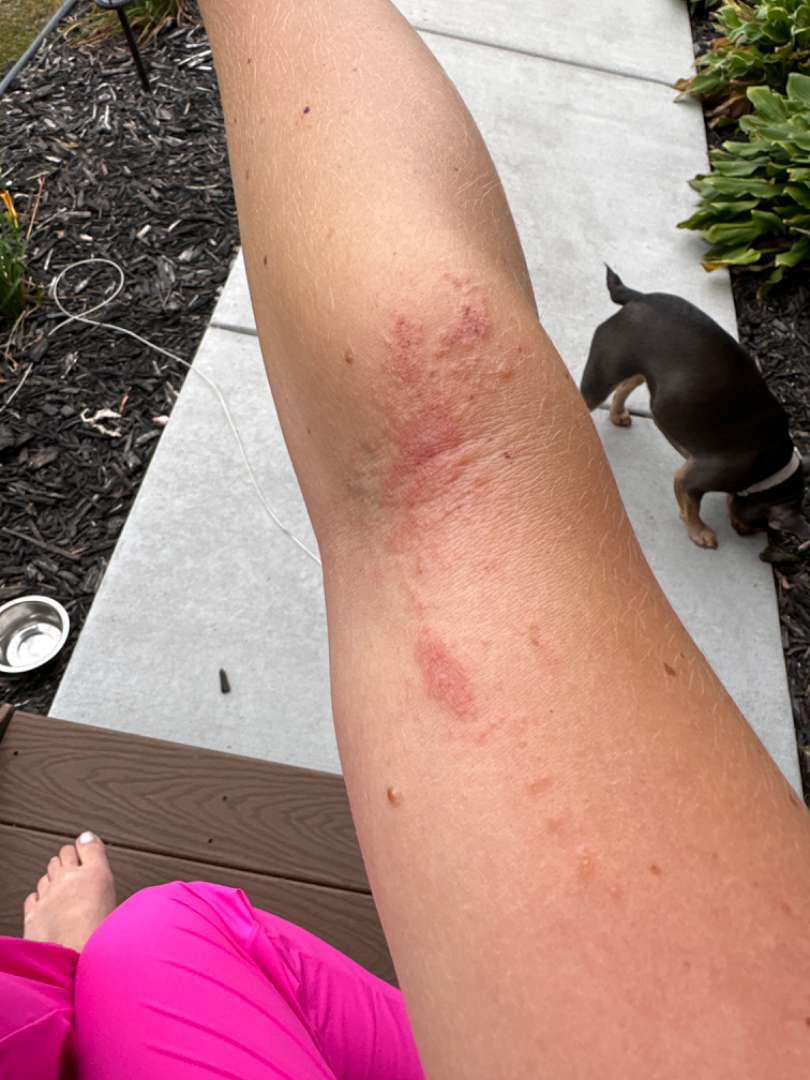Notes:
– impression — Eczema (most likely); Allergic Contact Dermatitis (considered)